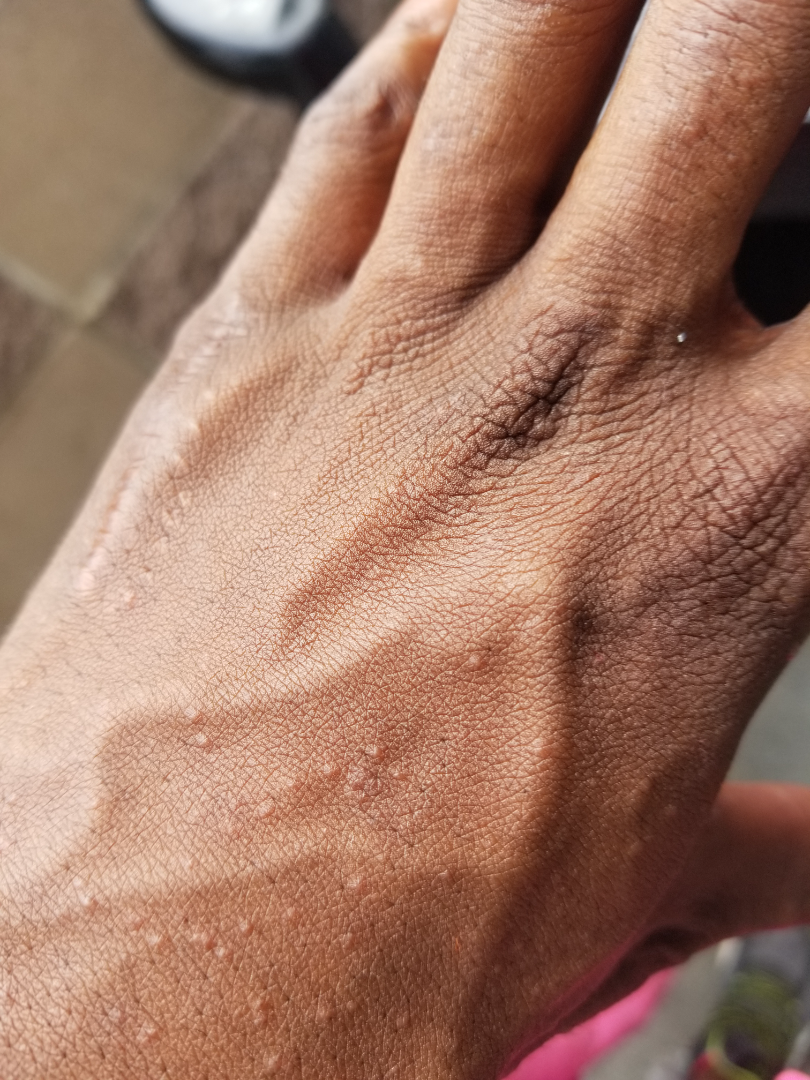Impression:
Diagnostic features were not clearly distinguishable in this photograph.
History:
This is a close-up image. The patient described the issue as a rash. Texture is reported as raised or bumpy. The patient reported no systemic symptoms. The condition has been present for less than one week. The lesion involves the back of the hand, arm and palm. The subject is 18–29, male. Symptoms reported: itching.